A dermoscopic close-up of a skin lesion: 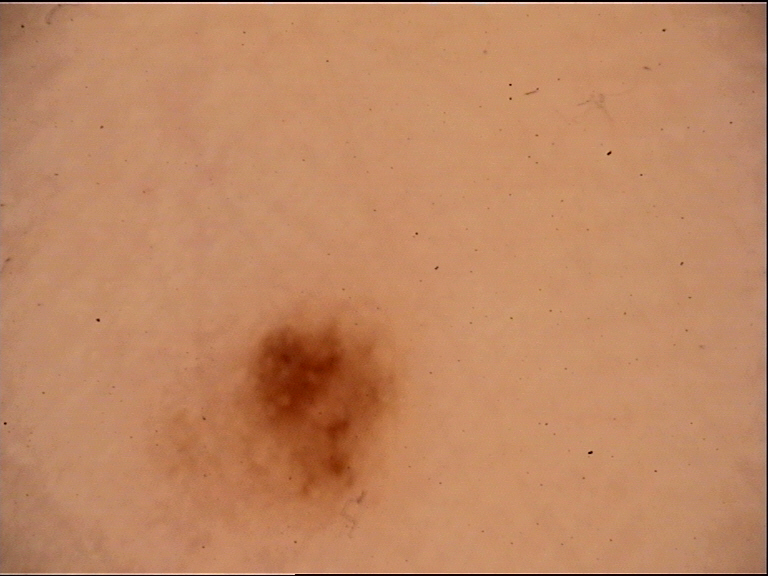Impression: Labeled as an acral dysplastic junctional nevus.